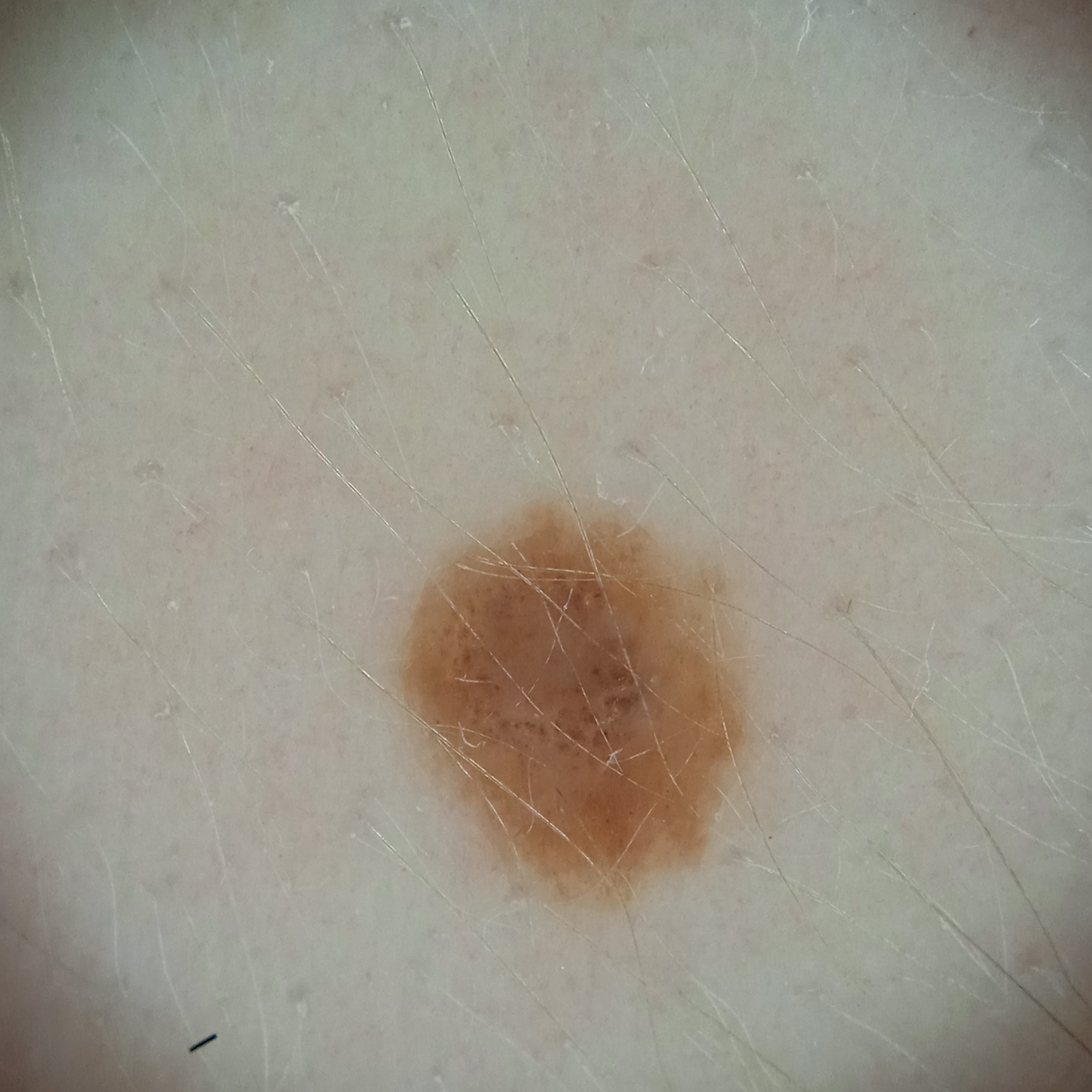Q: How does the patient's skin react to sun?
A: skin reddens with sun exposure
Q: What is the imaging modality?
A: dermoscopic image
Q: What is the patient's nevus burden?
A: a moderate number of melanocytic nevi
Q: Where is the lesion?
A: the torso
Q: How large is the lesion?
A: 4.4 mm
Q: What was the diagnosis?
A: melanocytic nevus (dermatologist consensus)